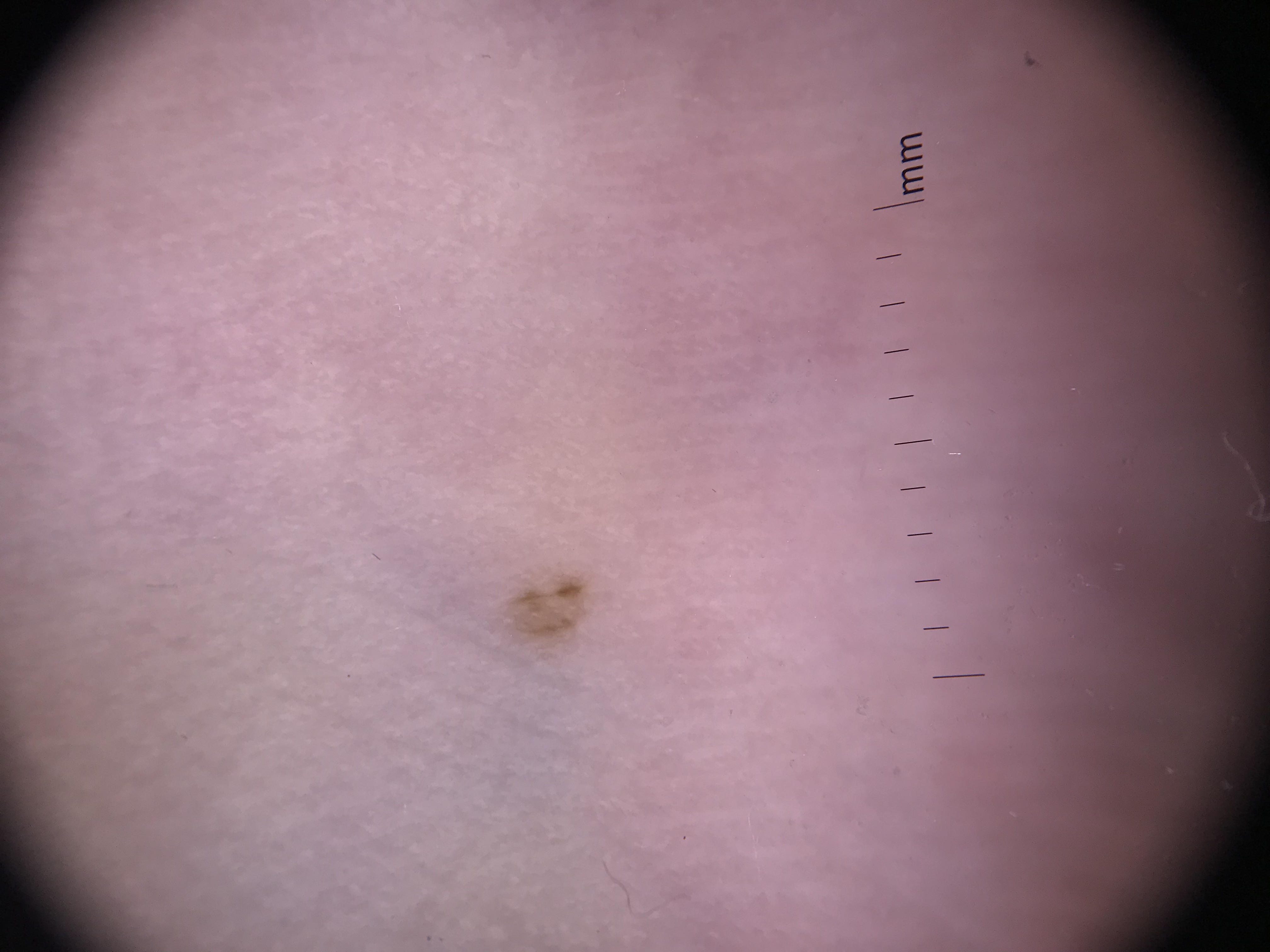Findings:
– classification · banal
– class · acral junctional nevus (expert consensus)